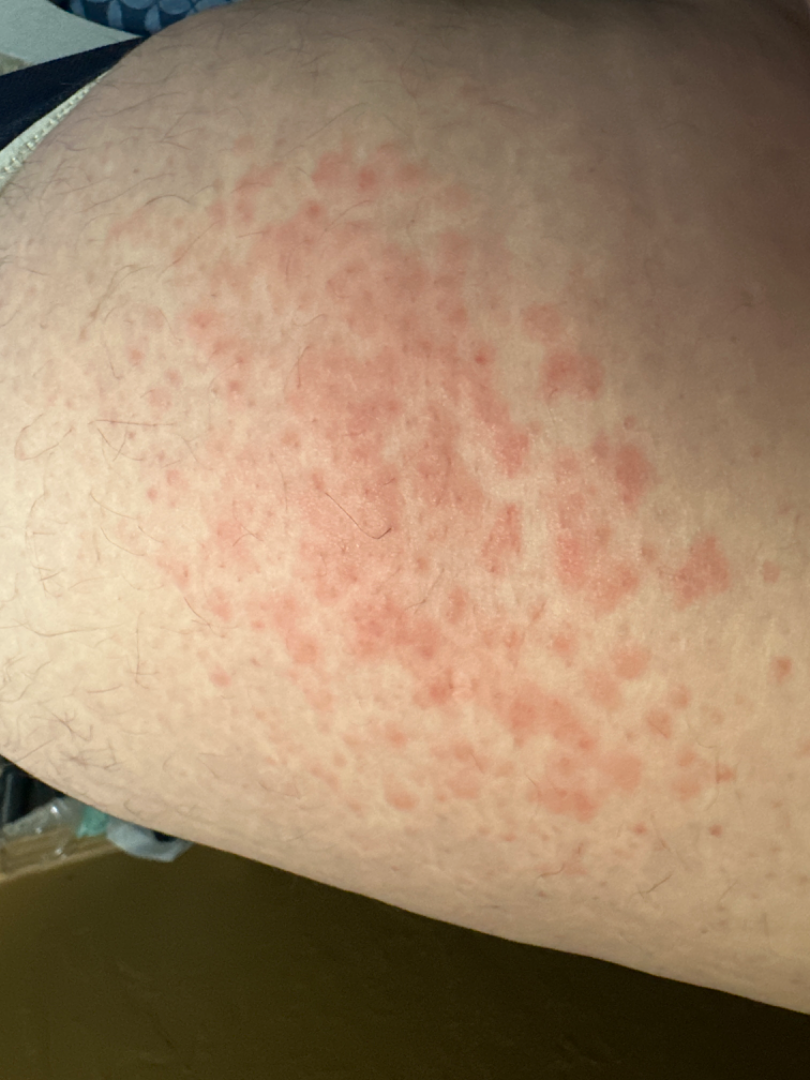Q: Could the case be diagnosed?
A: indeterminate from the photograph
Q: How was the photo taken?
A: close-up